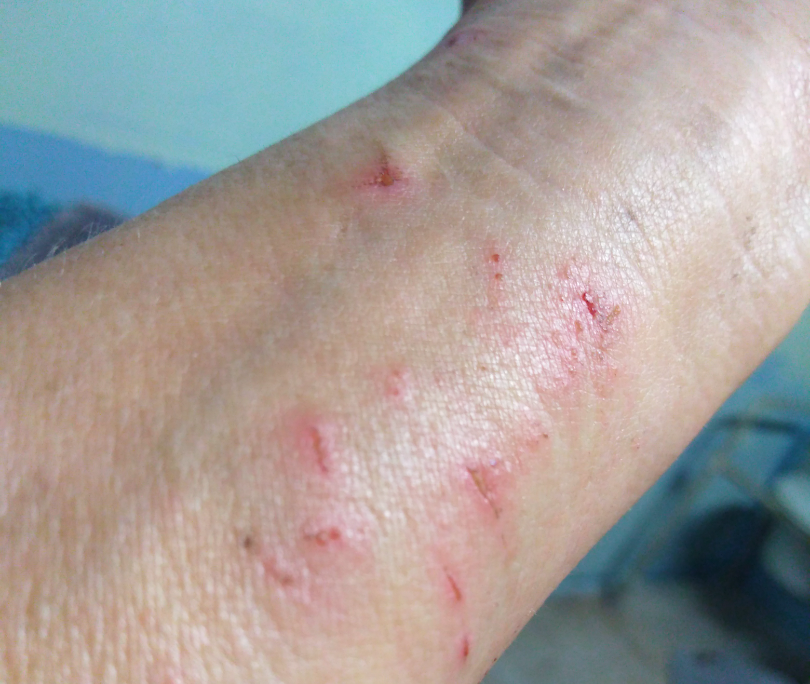| key | value |
|---|---|
| impression | Prurigo nodularis (leading) |